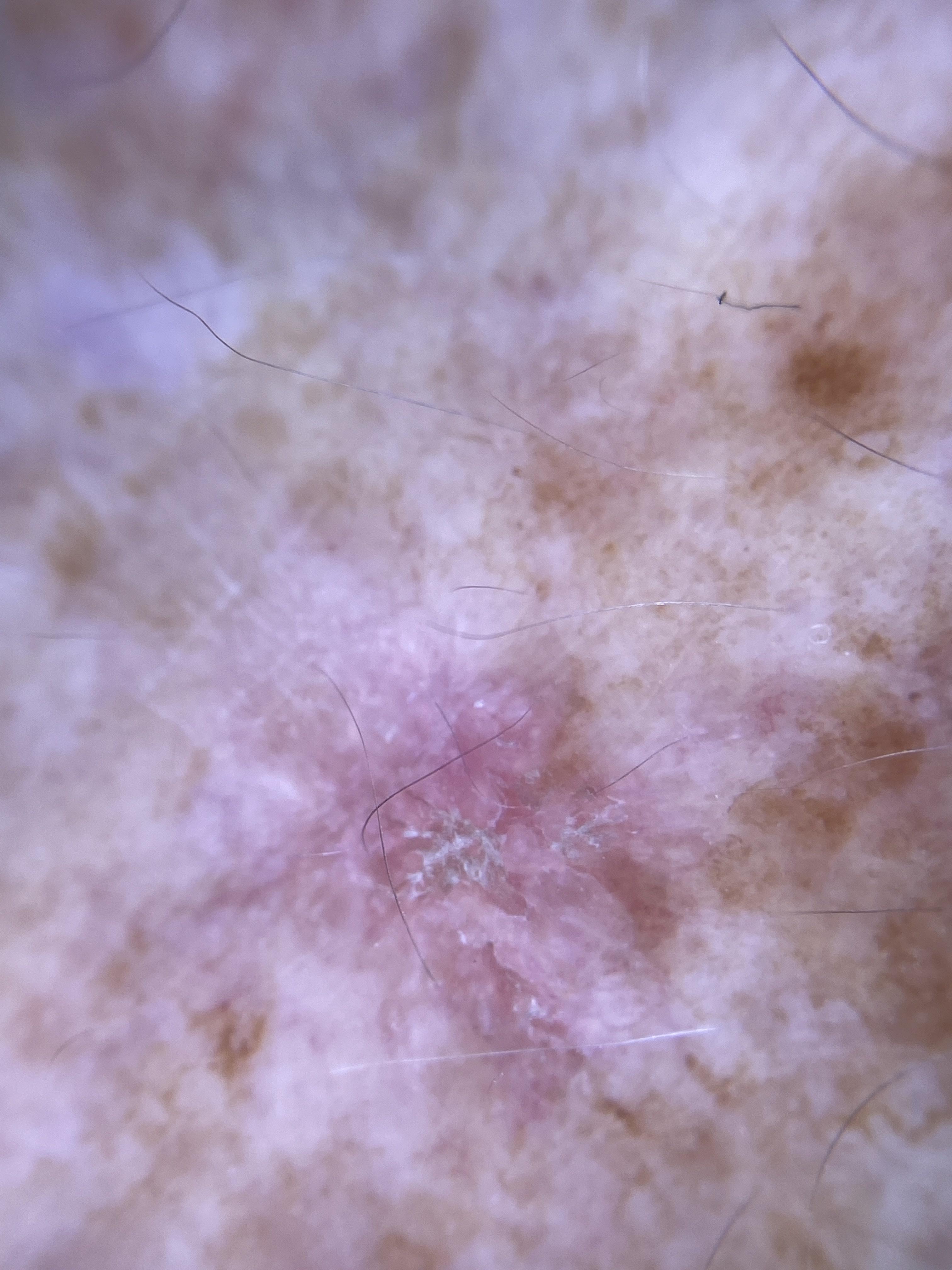A female patient aged 78 to 82. The patient is FST II. On biopsy, the diagnosis was a squamous cell carcinoma.